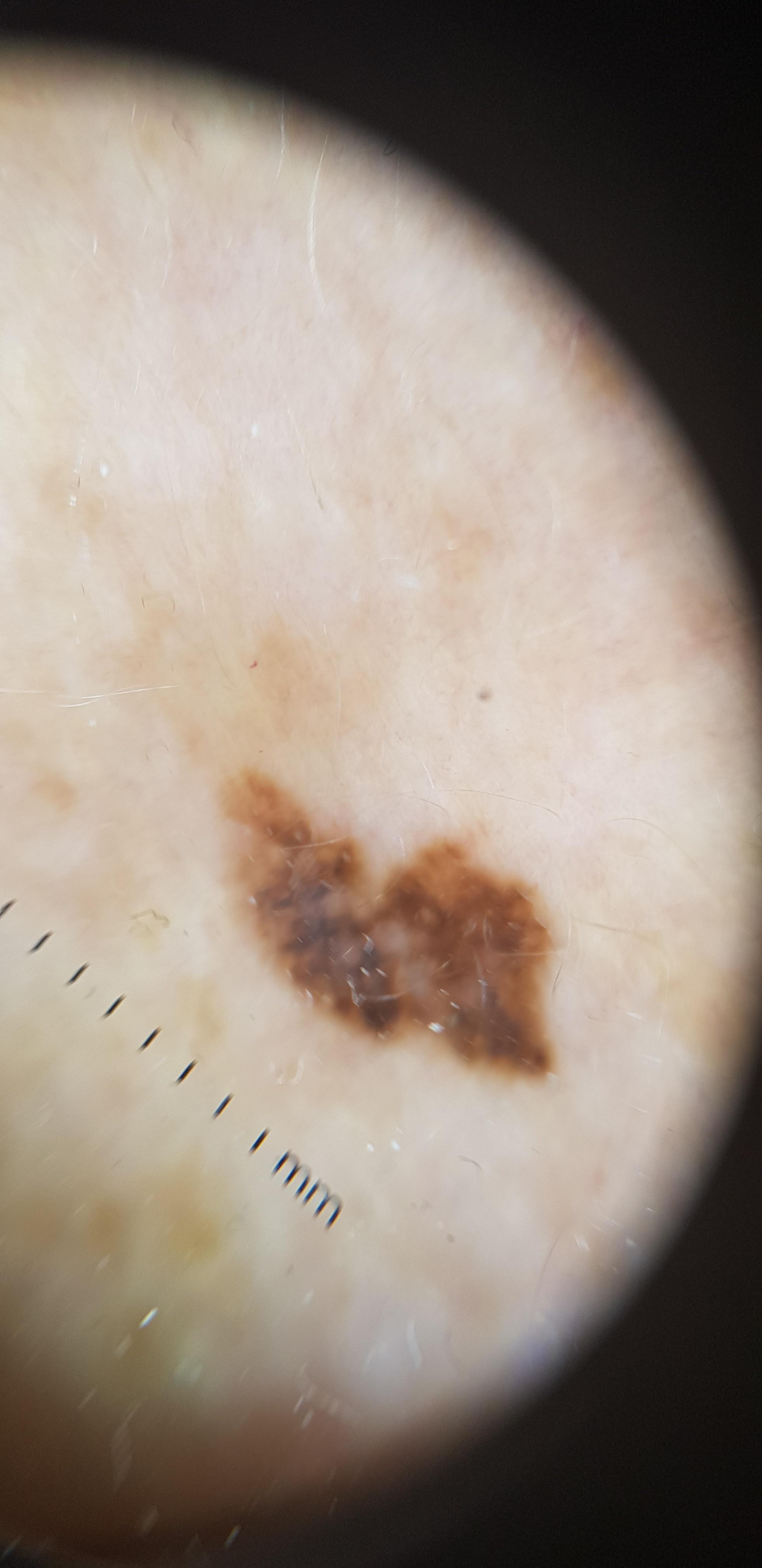A skin lesion imaged with contact-polarized dermoscopy.
A female patient aged approximately 80.
Located on an upper extremity.
Confirmed on histopathology as a benign, melanocytic lesion — a nevus.